This is a close-up image · reported duration is one to four weeks · texture is reported as raised or bumpy · Fitzpatrick I.
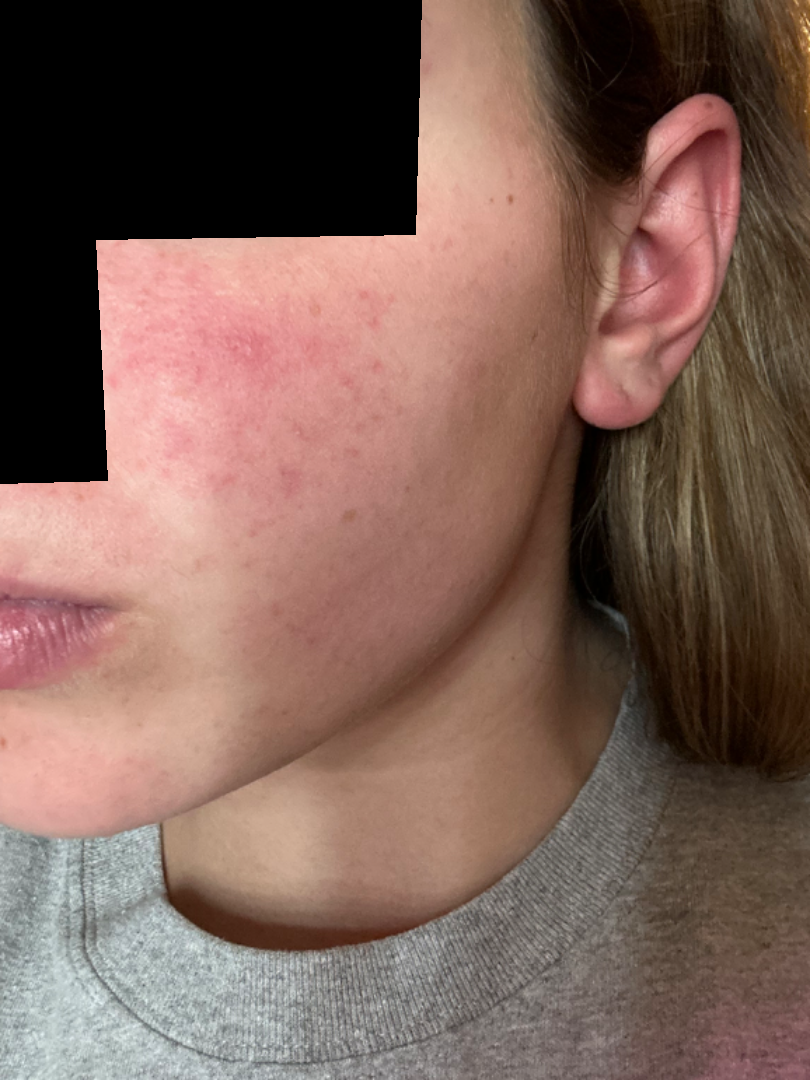Assessment:
On photographic review: most consistent with Rosacea.